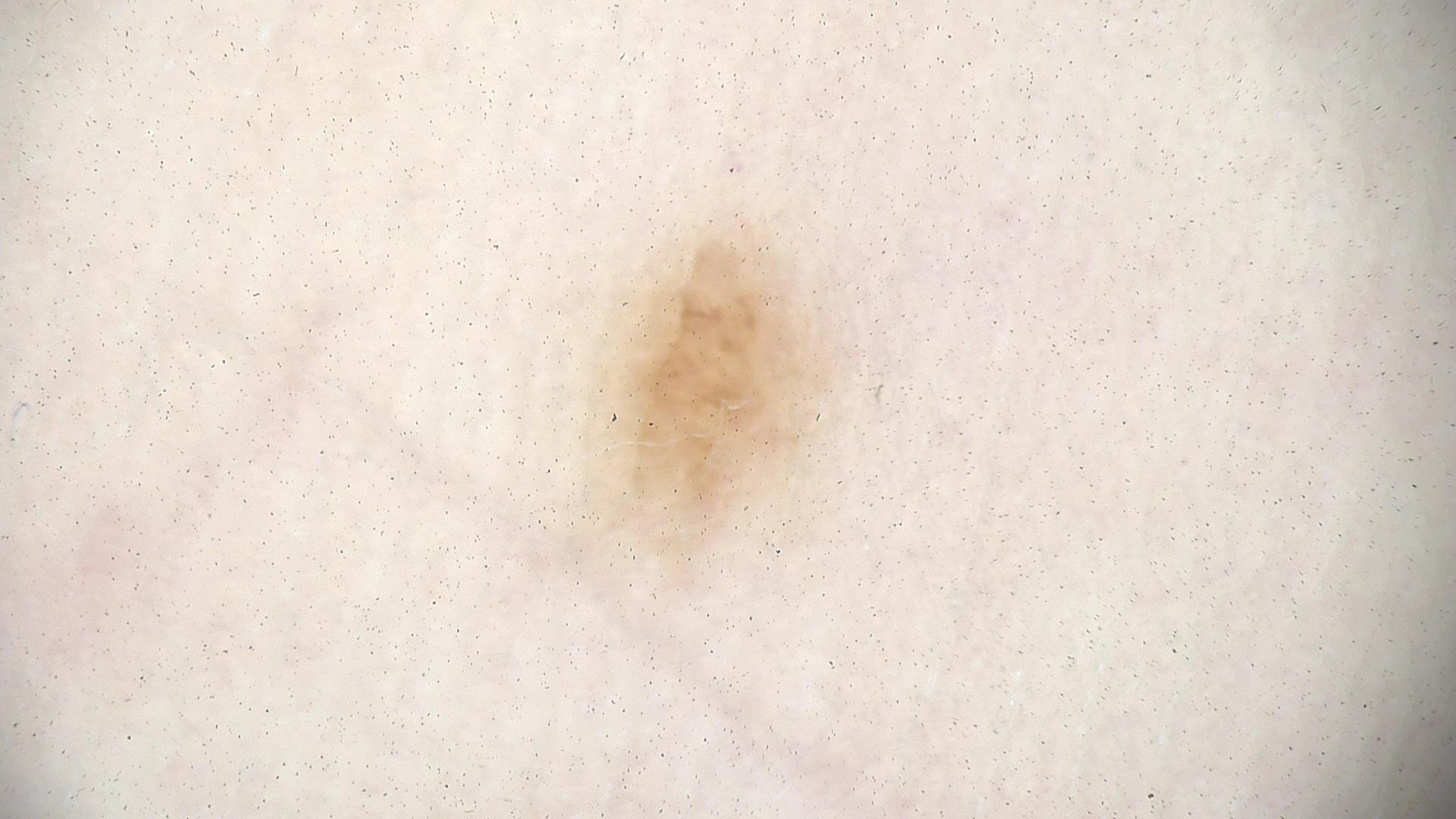<dermoscopy>
  <image>dermoscopy</image>
  <diagnosis>
    <name>acral dysplastic junctional nevus</name>
    <code>ajd</code>
    <malignancy>benign</malignancy>
    <super_class>melanocytic</super_class>
    <confirmation>expert consensus</confirmation>
  </diagnosis>
</dermoscopy>